The photograph is a close-up of the affected area — 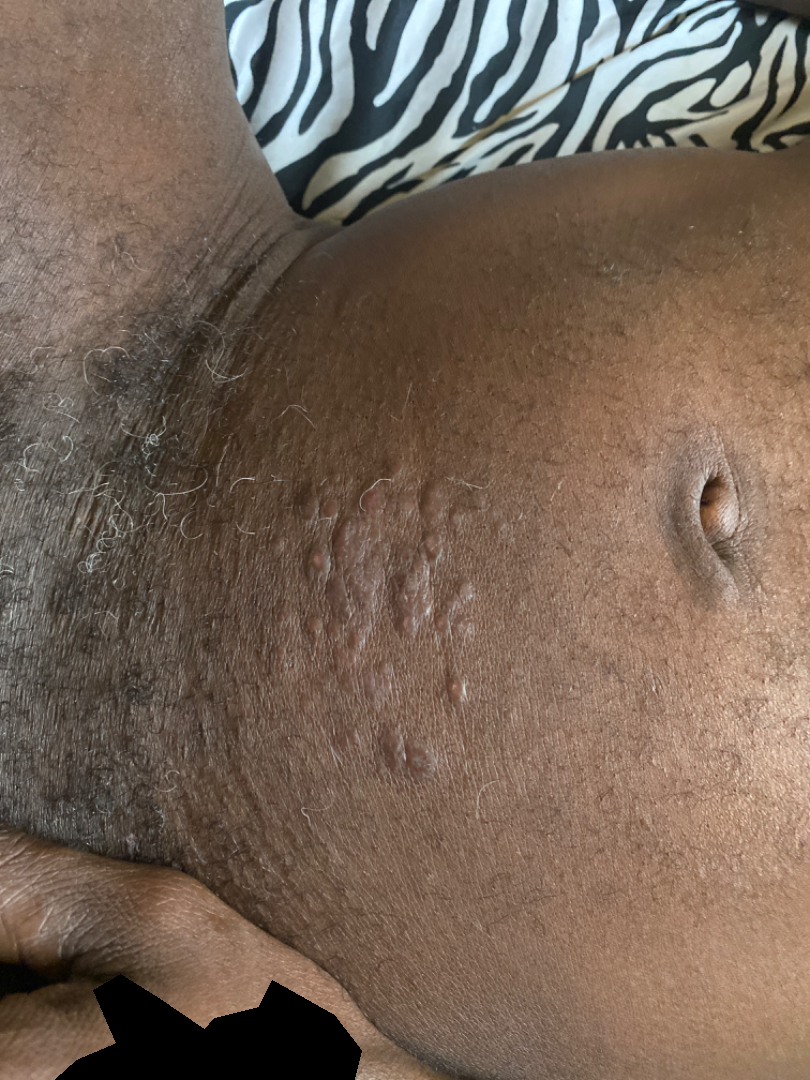assessment: the leading impression is Allergic Contact Dermatitis; with consideration of Eczema; also on the differential is Verruca vulgaris